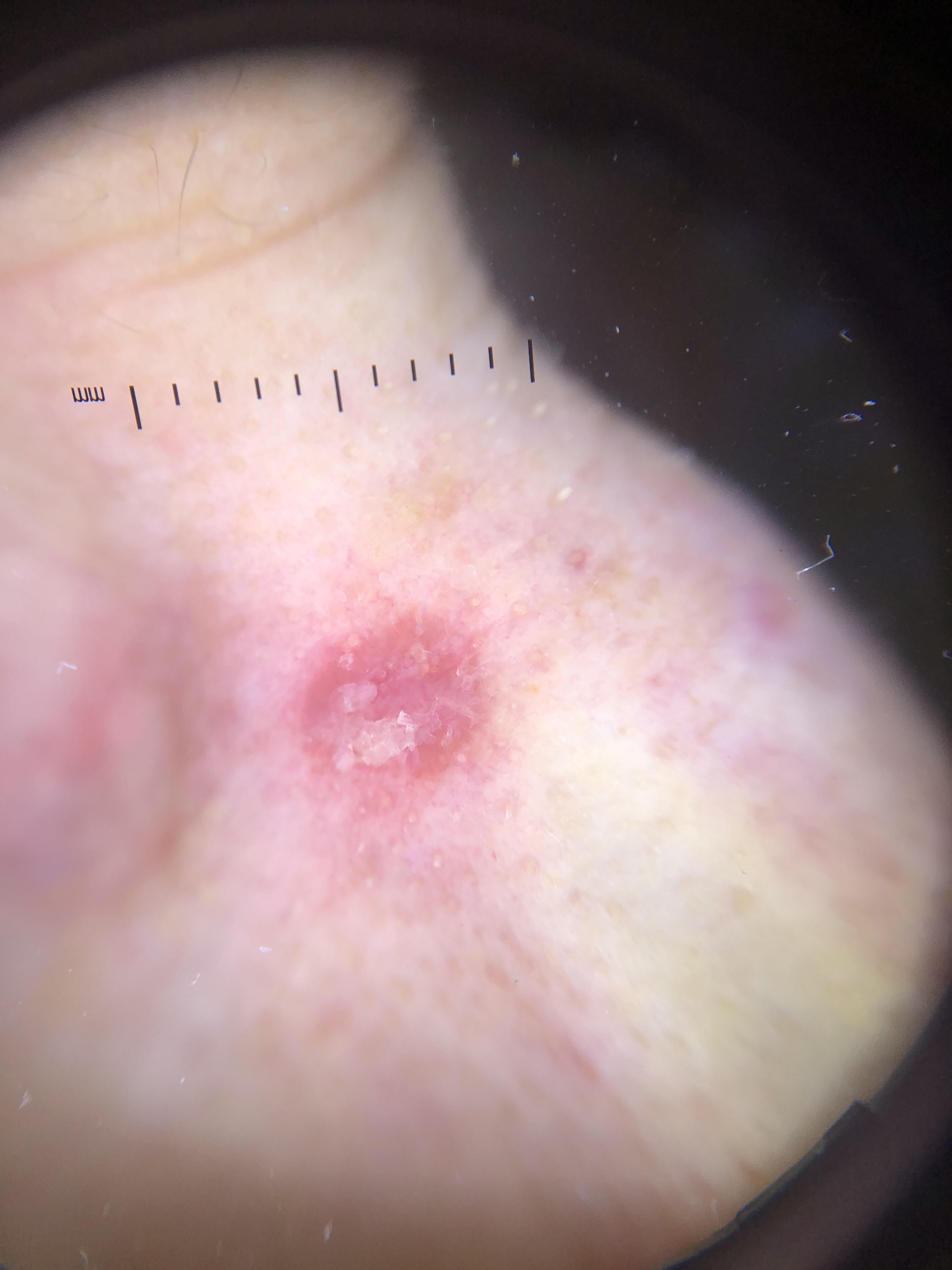A female patient aged approximately 80.
The lesion is on the head or neck.
Histopathologically confirmed as a basal cell carcinoma.